Texture is reported as raised or bumpy. Present for one to three months. Self-categorized by the patient as a rash. Fitzpatrick I. The affected area is the top or side of the foot and leg. Male patient, age 40–49. The patient indicates itching and bothersome appearance. The photo was captured at a distance:
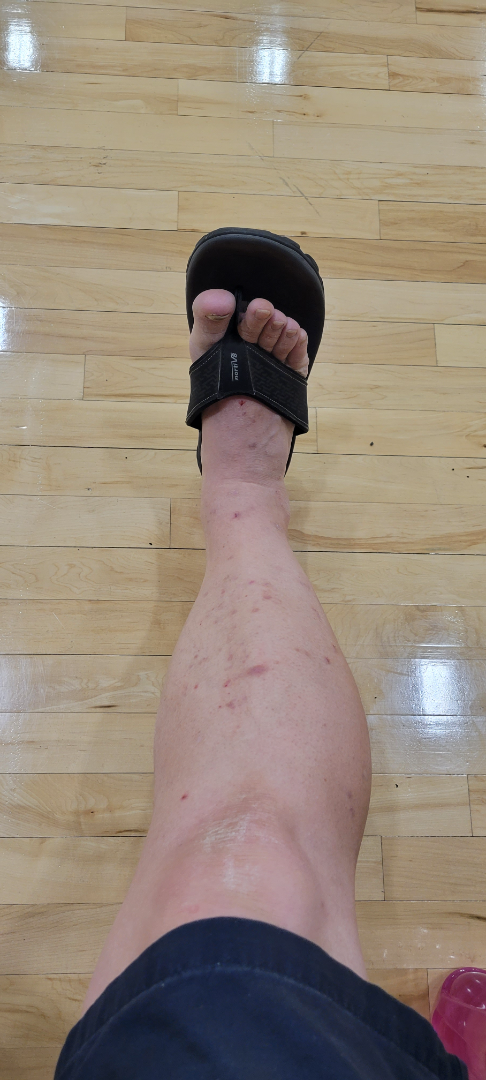Case summary:
- differential diagnosis: the leading consideration is Folliculitis; possibly Insect Bite; less probable is Eczema